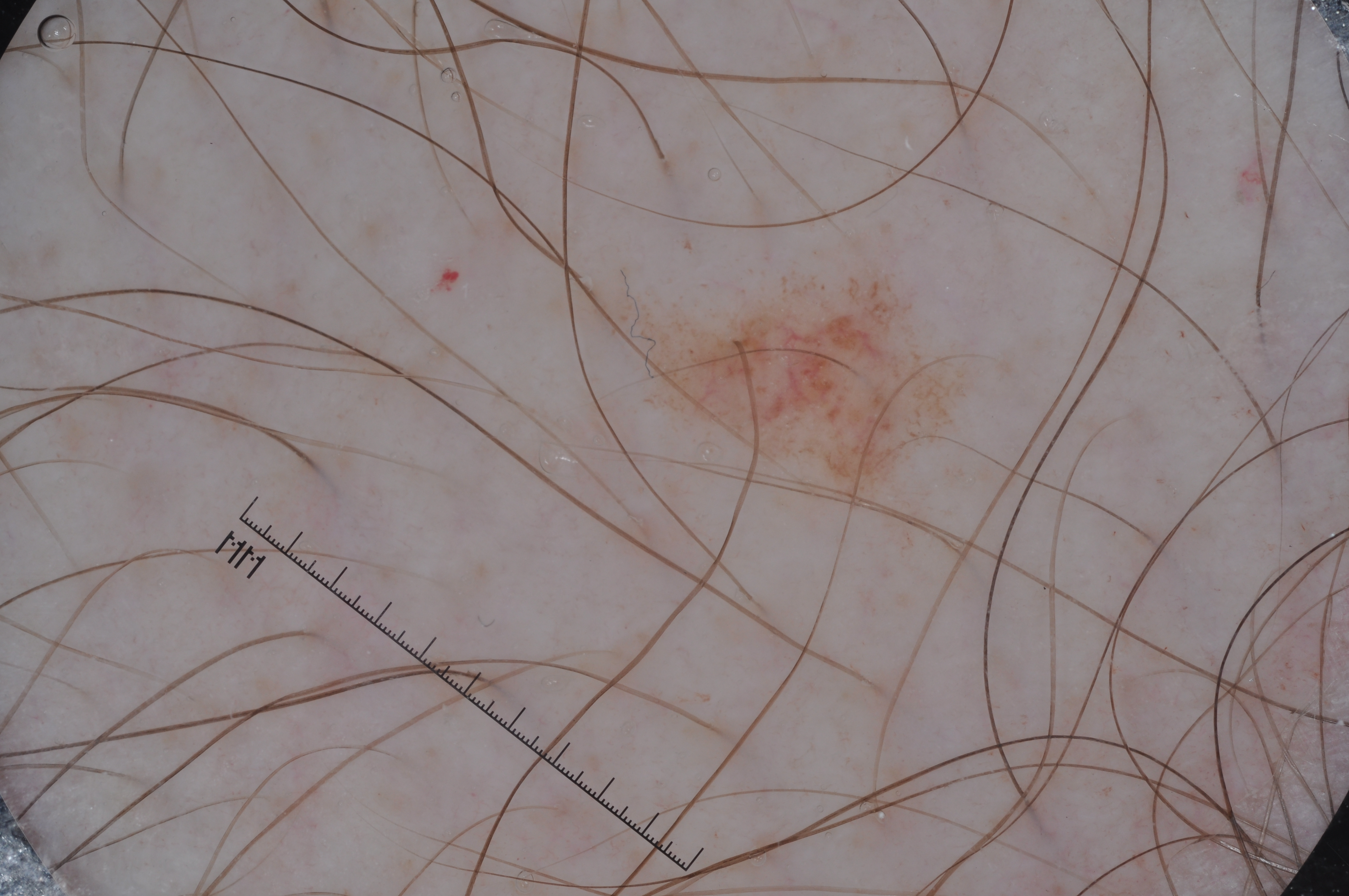Dermoscopy of a skin lesion. The lesion is small relative to the field of view. The lesion occupies the region bbox(571, 242, 983, 519). Dermoscopic review identifies pigment network. The lesion was assessed as a melanocytic nevus.